A dermoscopy image of a single skin lesion: 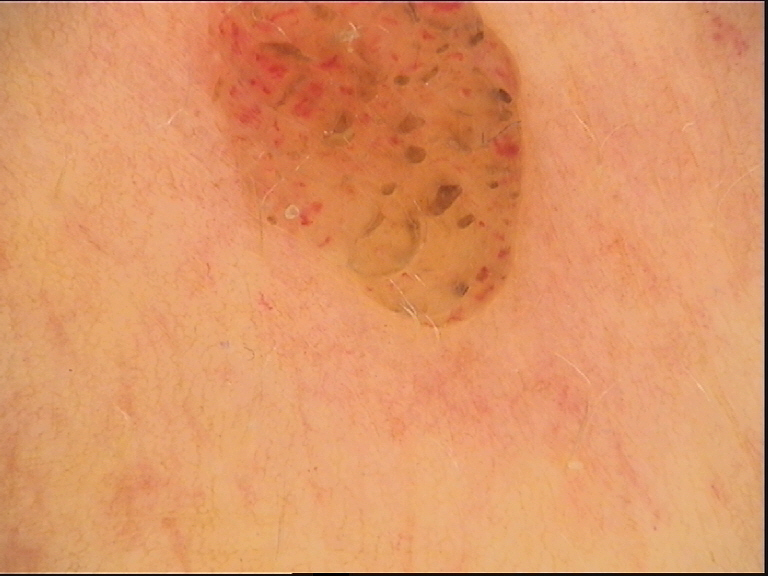This is a banal lesion. The diagnostic label was a dermal nevus.